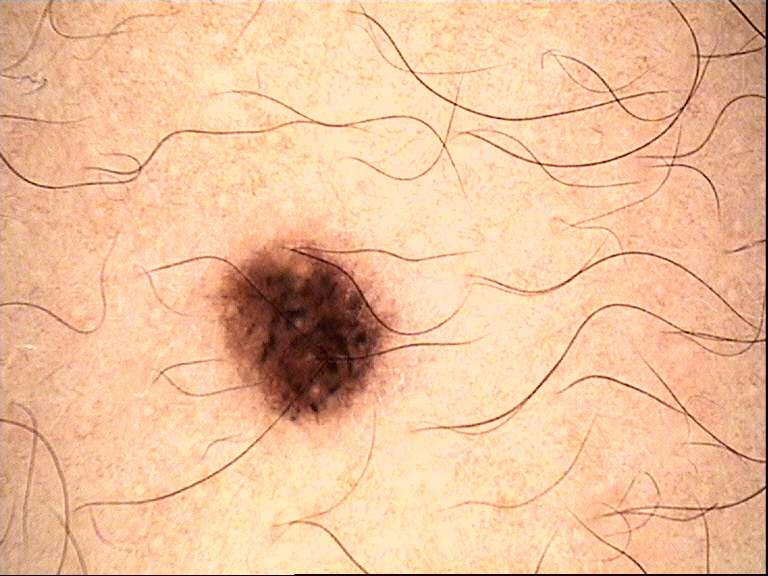Impression: Classified as a benign lesion — a dysplastic junctional nevus.